A dermatoscopic image of a skin lesion.
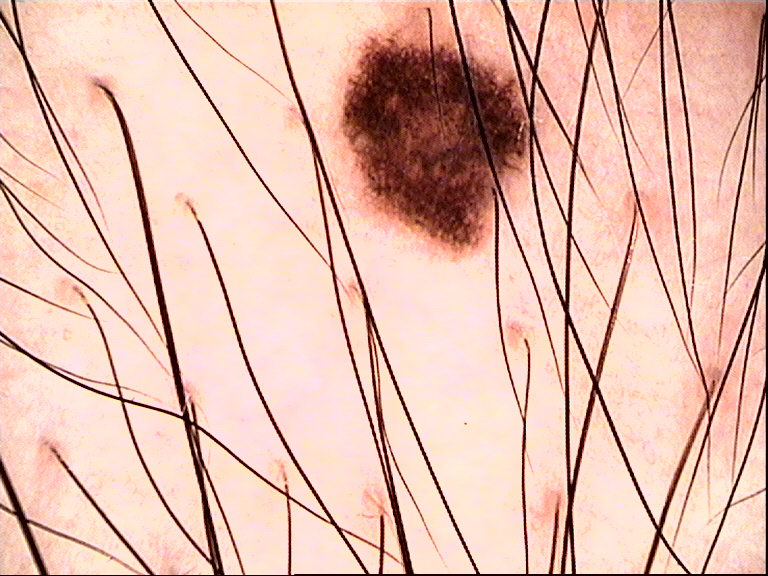Conclusion: Classified as a dysplastic junctional nevus.